Located on the arm, the patient reports the lesion is raised or bumpy, symptoms reported: itching, the condition has been present for about one day, the patient described the issue as a rash, the patient reported no systemic symptoms, the photograph was taken at a distance, skin tone: Fitzpatrick I; non-clinician graders estimated 2 on the Monk skin tone scale, the subject is a female aged 60–69: 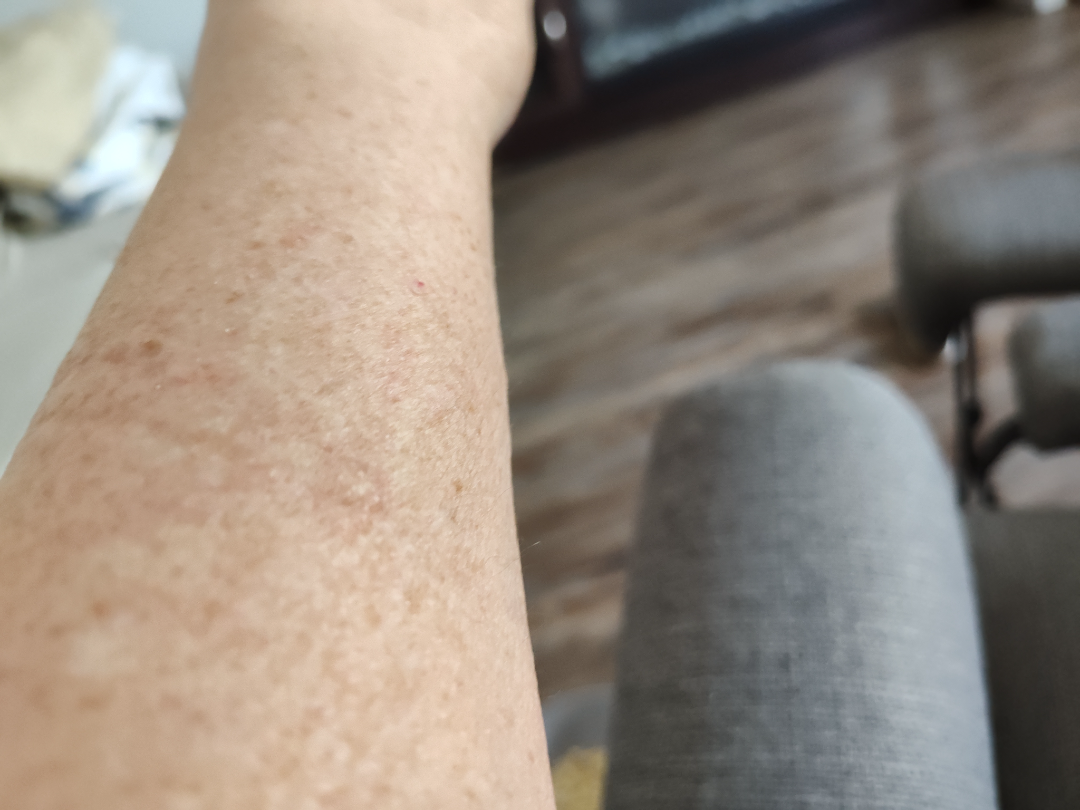| field | value |
|---|---|
| differential | Eczema (favored); Irritant Contact Dermatitis (possible); Pigmented purpuric eruption (lower probability); Allergic Contact Dermatitis (lower probability) |